A male subject 51 years old — 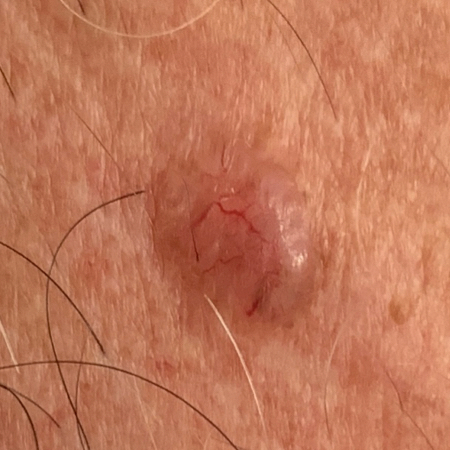| key | value |
|---|---|
| patient-reported symptoms | pain, elevation, itching, bleeding |
| pathology | basal cell carcinoma (biopsy-proven) |